Located on the leg; the photograph is a close-up of the affected area; the patient is a female aged 40–49:
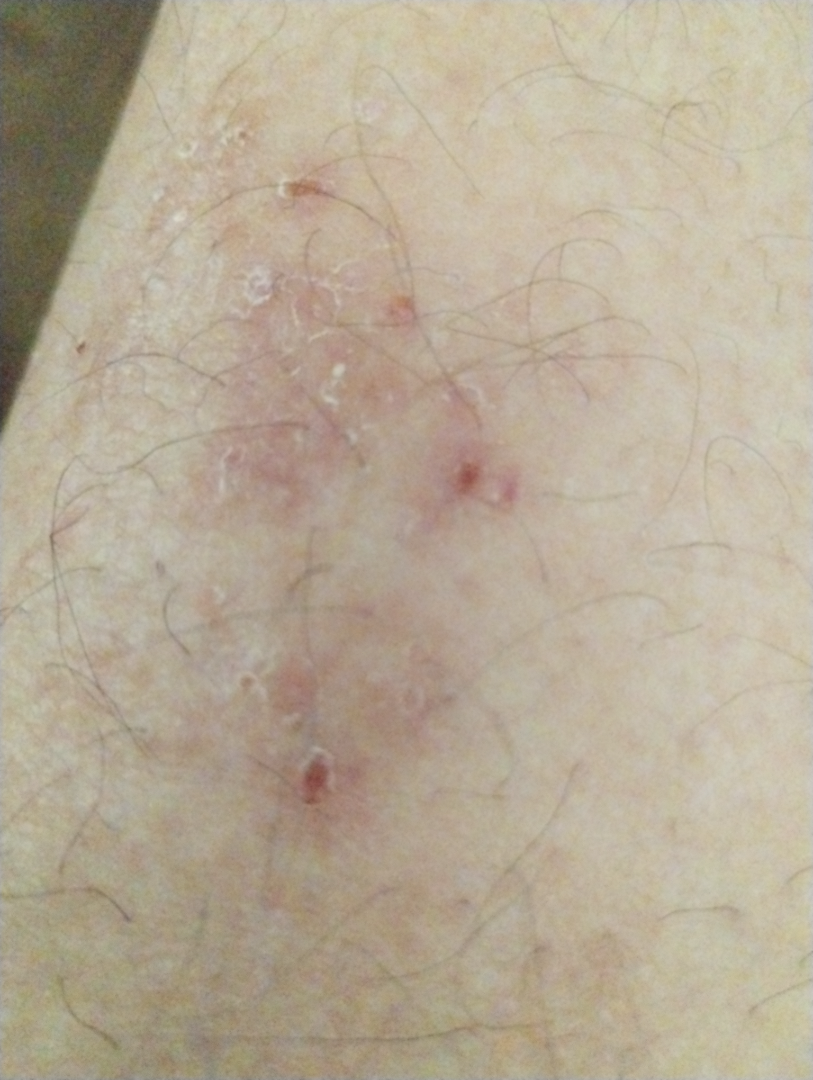The case was difficult to assess from the available photograph.